A male patient 59 years old: 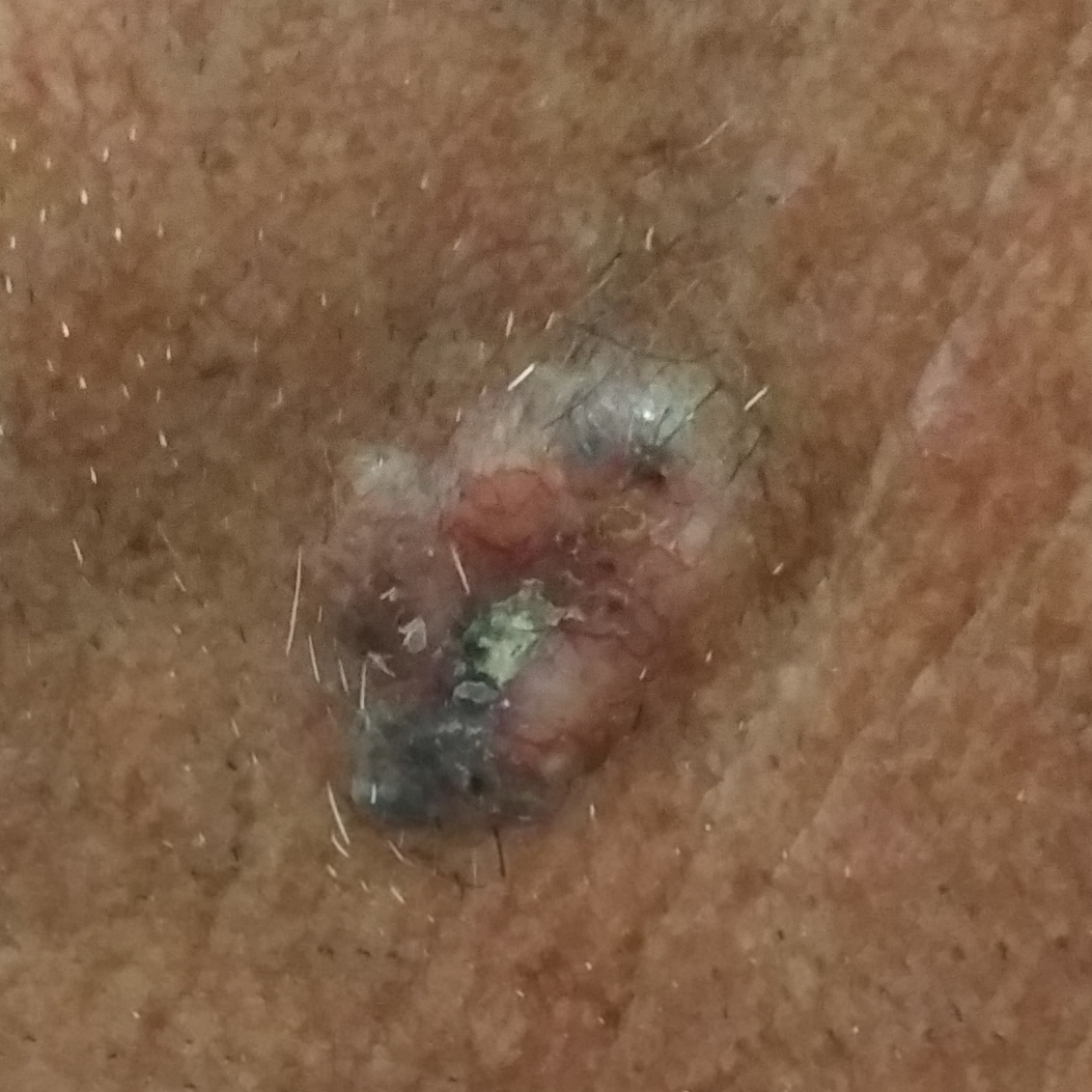Case summary: The lesion was found on the neck. The patient describes that the lesion is elevated, itches, hurts, has grown, and has bled, but has not changed. Conclusion: Histopathology confirmed a basal cell carcinoma.